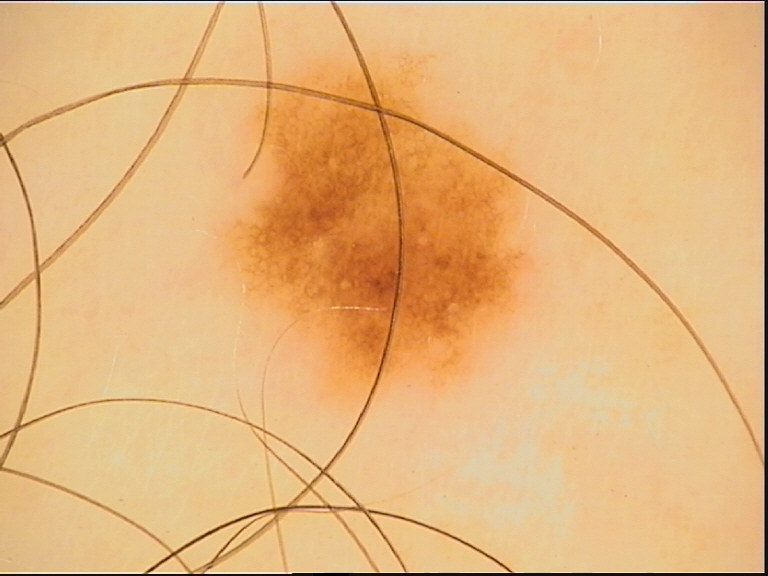Classified as a dysplastic junctional nevus.